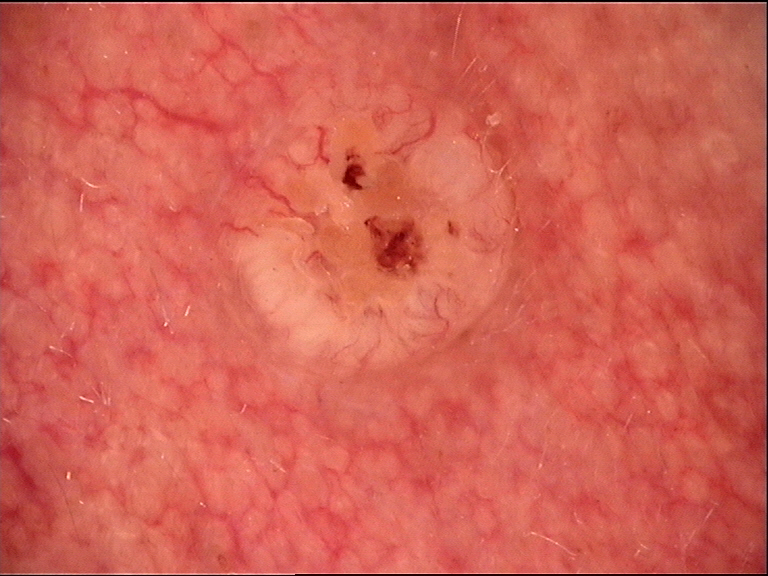Summary: A dermoscopy image of a single skin lesion. The morphology is that of a keratinocytic lesion. Conclusion: Confirmed on histopathology as a skin cancer — a basal cell carcinoma.